Reported lesion symptoms include enlargement, burning and itching. Skin tone: FST IV; lay reviewers estimated Monk Skin Tone 3. The arm is involved. The patient reports the condition has been present for one to four weeks. The patient described the issue as a rash. Texture is reported as rough or flaky. The photograph was taken at a distance. Female contributor, age 50–59 — 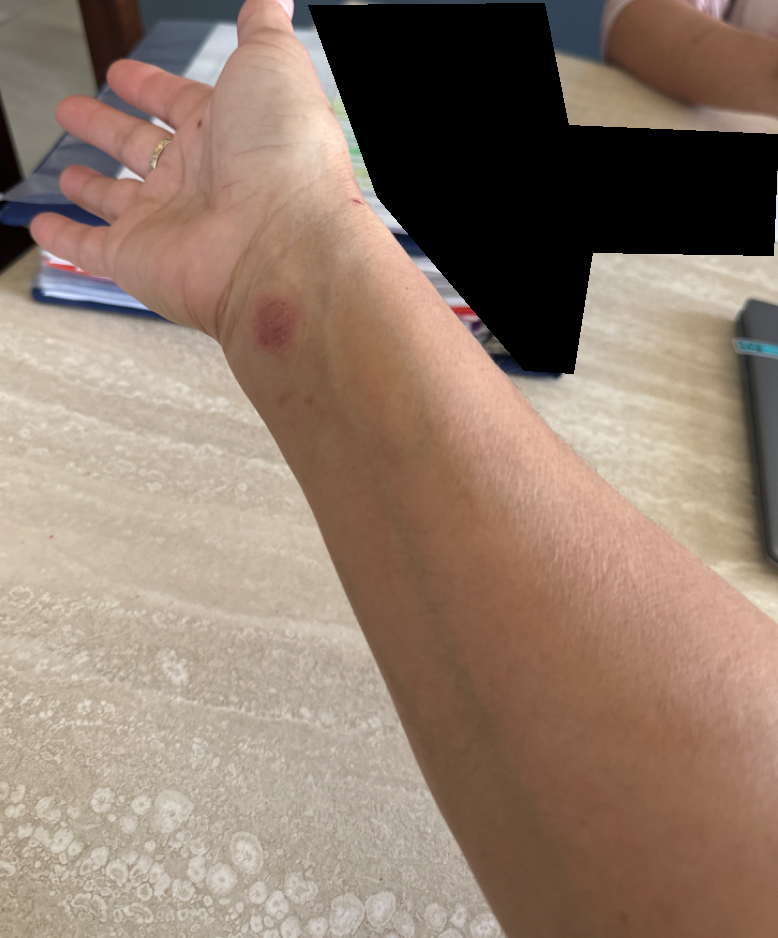Assessment: On independent review by the dermatologists: the leading impression is Allergic Contact Dermatitis; a more distant consideration is Abscess; less likely is Cyst; less probable is Eczema; a remote consideration is Acute and chronic dermatitis; lower on the differential is Irritant Contact Dermatitis.